A skin lesion imaged with a dermatoscope.
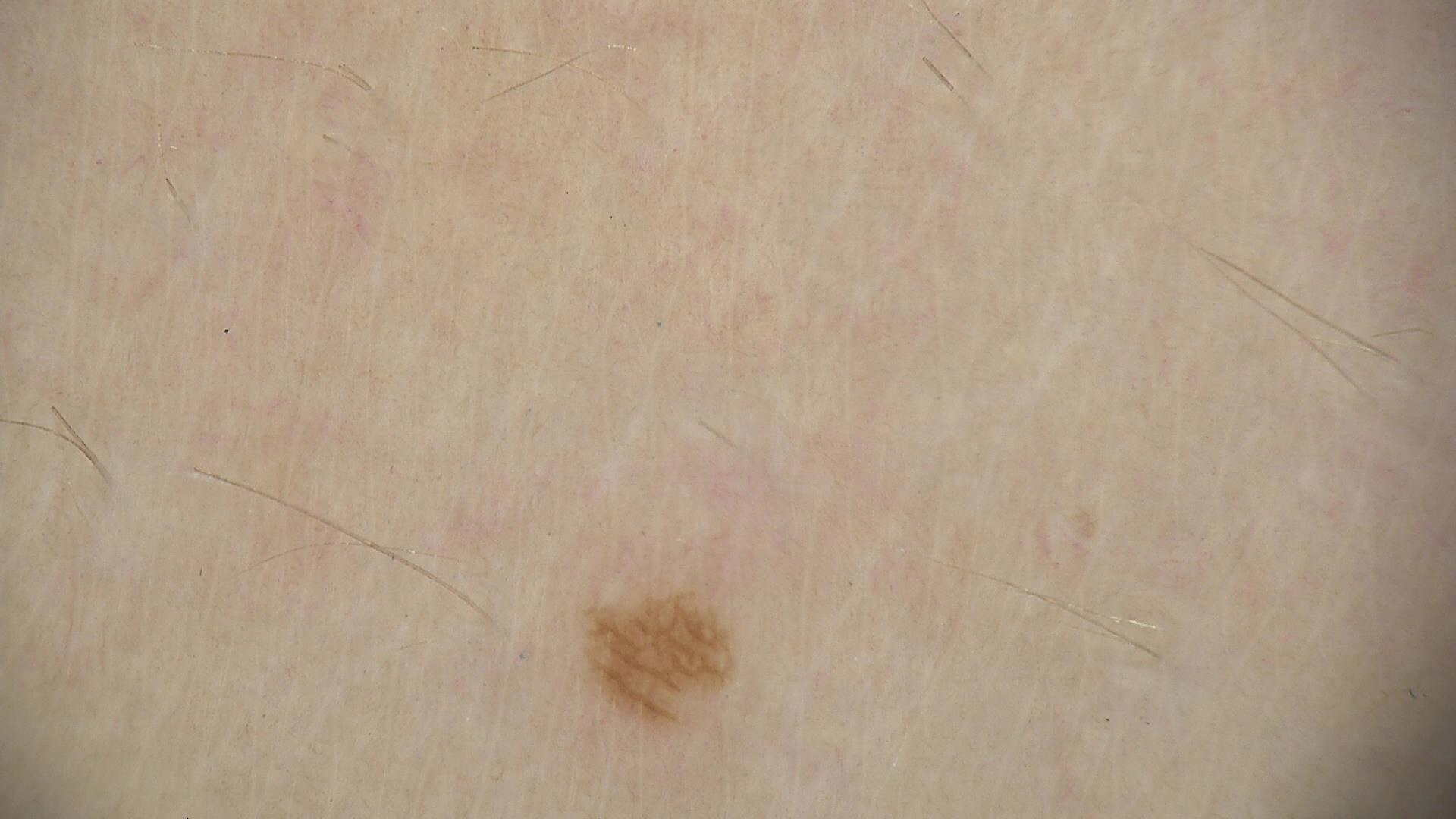The morphology is that of a banal lesion.
Consistent with a junctional nevus.